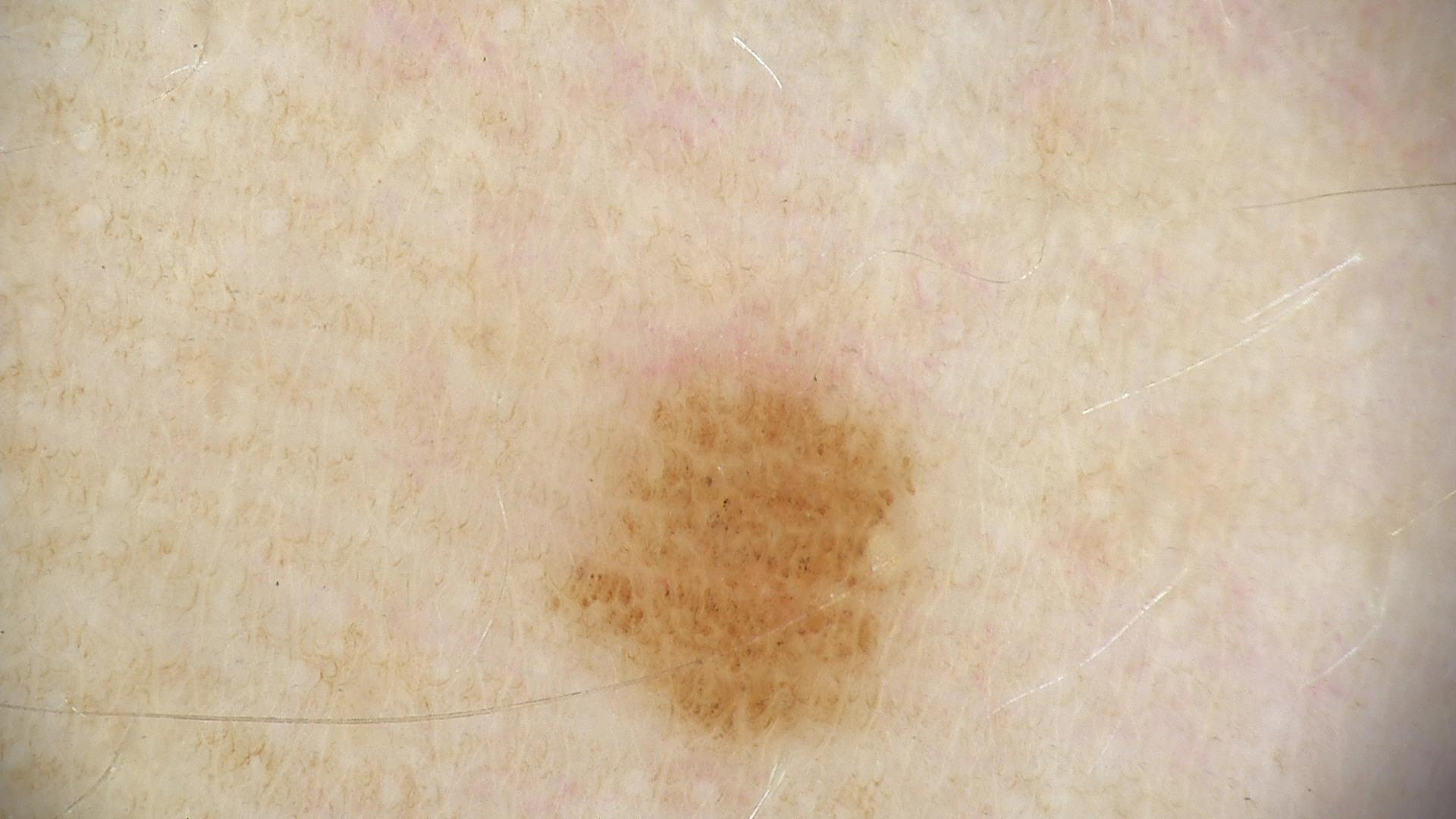diagnostic label: dysplastic junctional nevus (expert consensus).